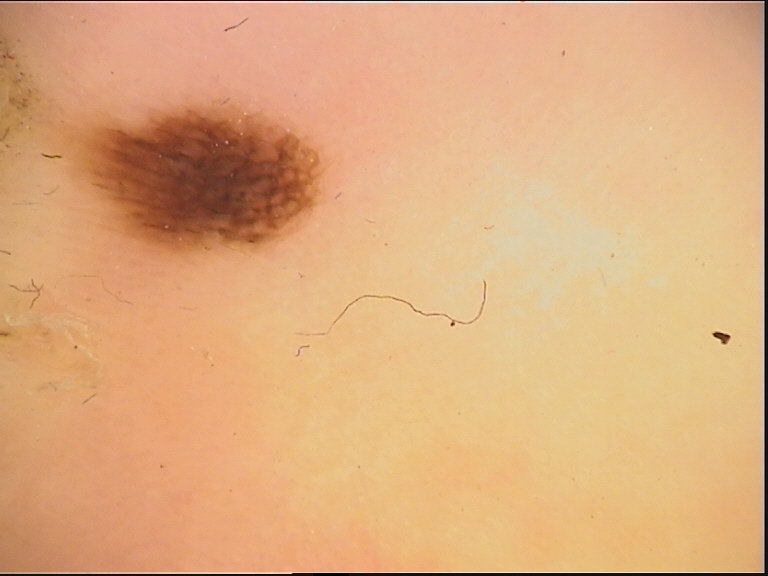Case: A dermoscopic close-up of a skin lesion. Conclusion: The diagnostic label was a benign lesion — an acral dysplastic junctional nevus.